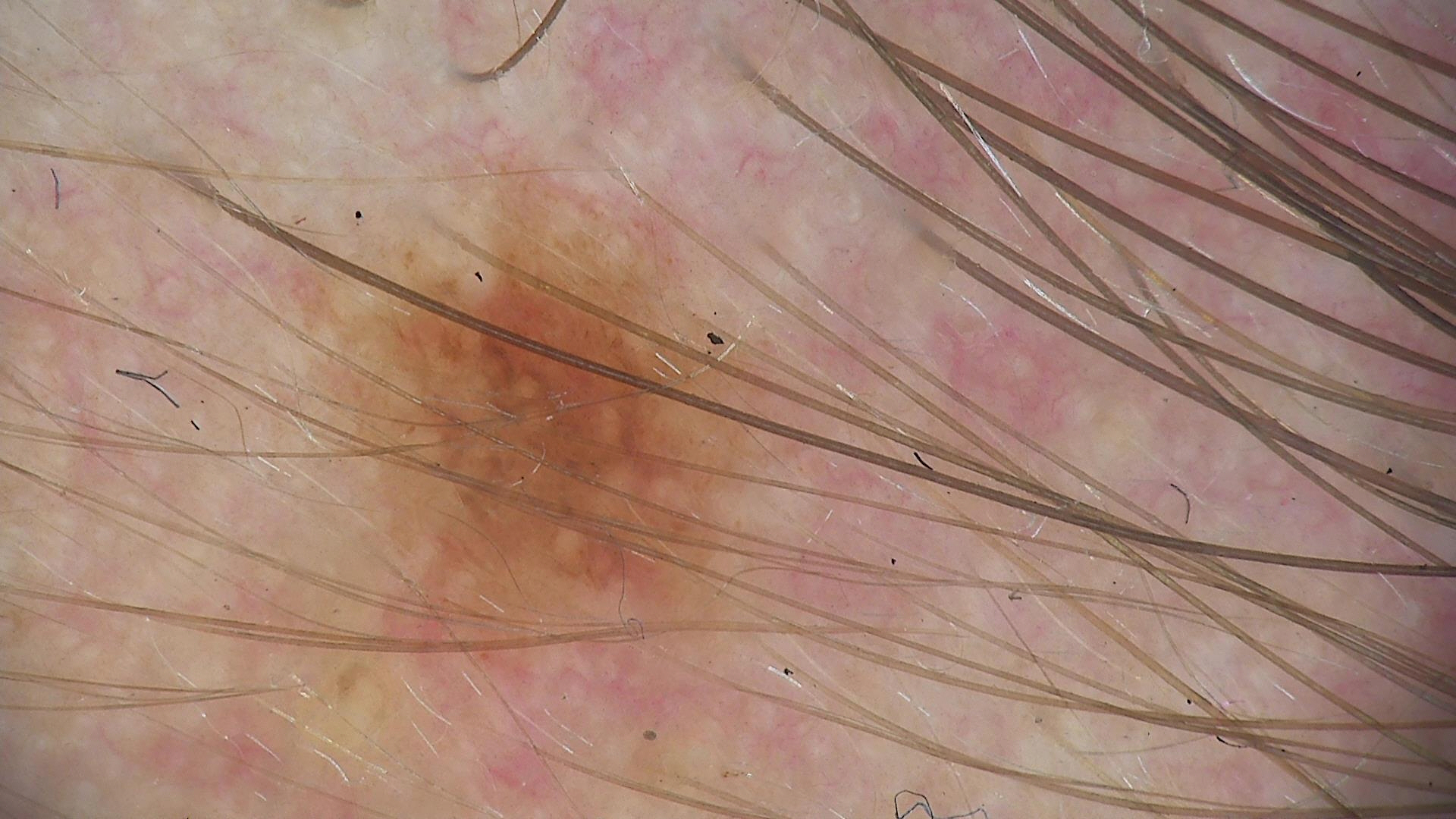label=dysplastic junctional nevus (expert consensus)